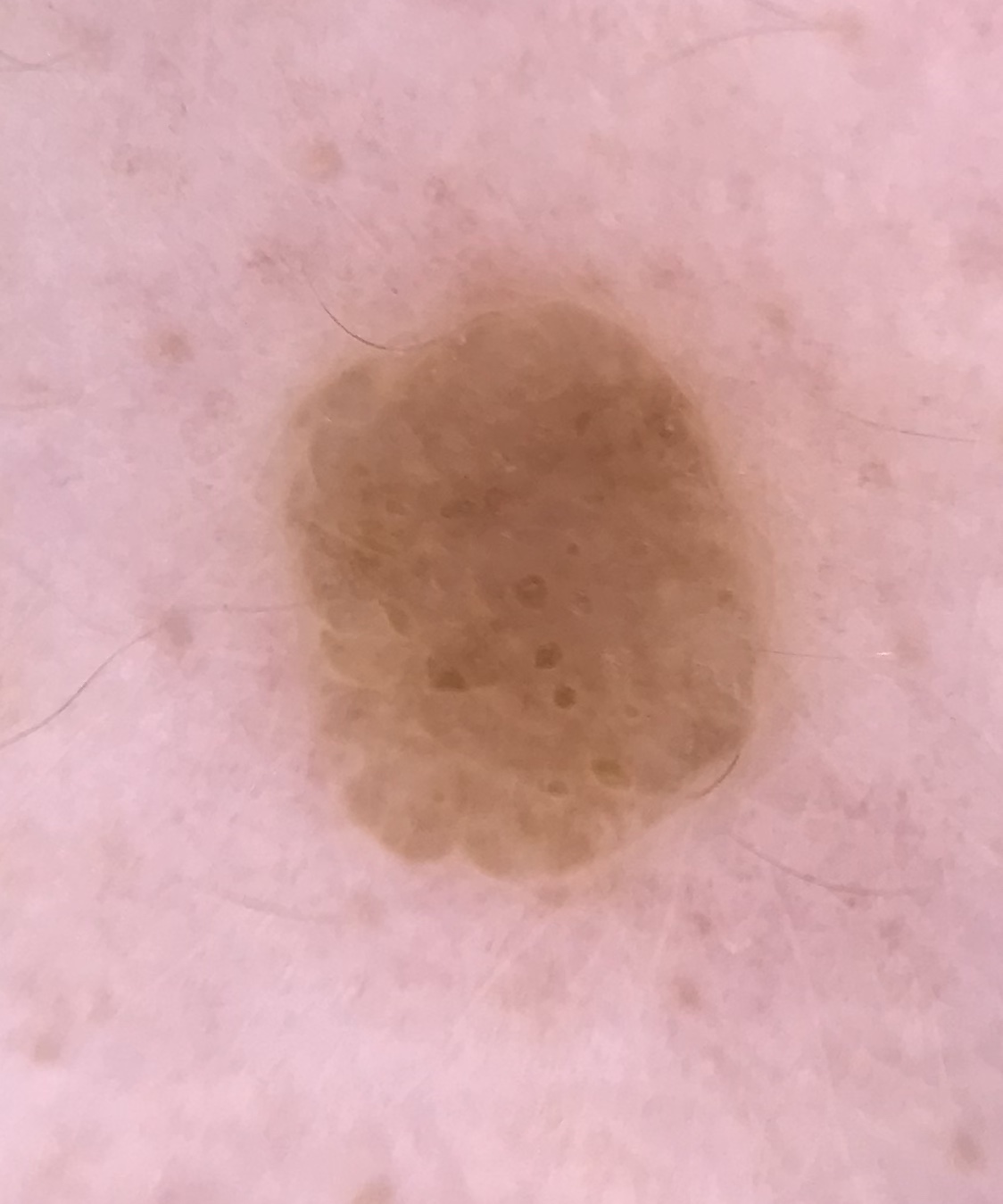Dermoscopy of a skin lesion. The architecture is that of a keratinocytic lesion. Diagnosed as a seborrheic keratosis.